A male subject · a dermoscopic view of a skin lesion.
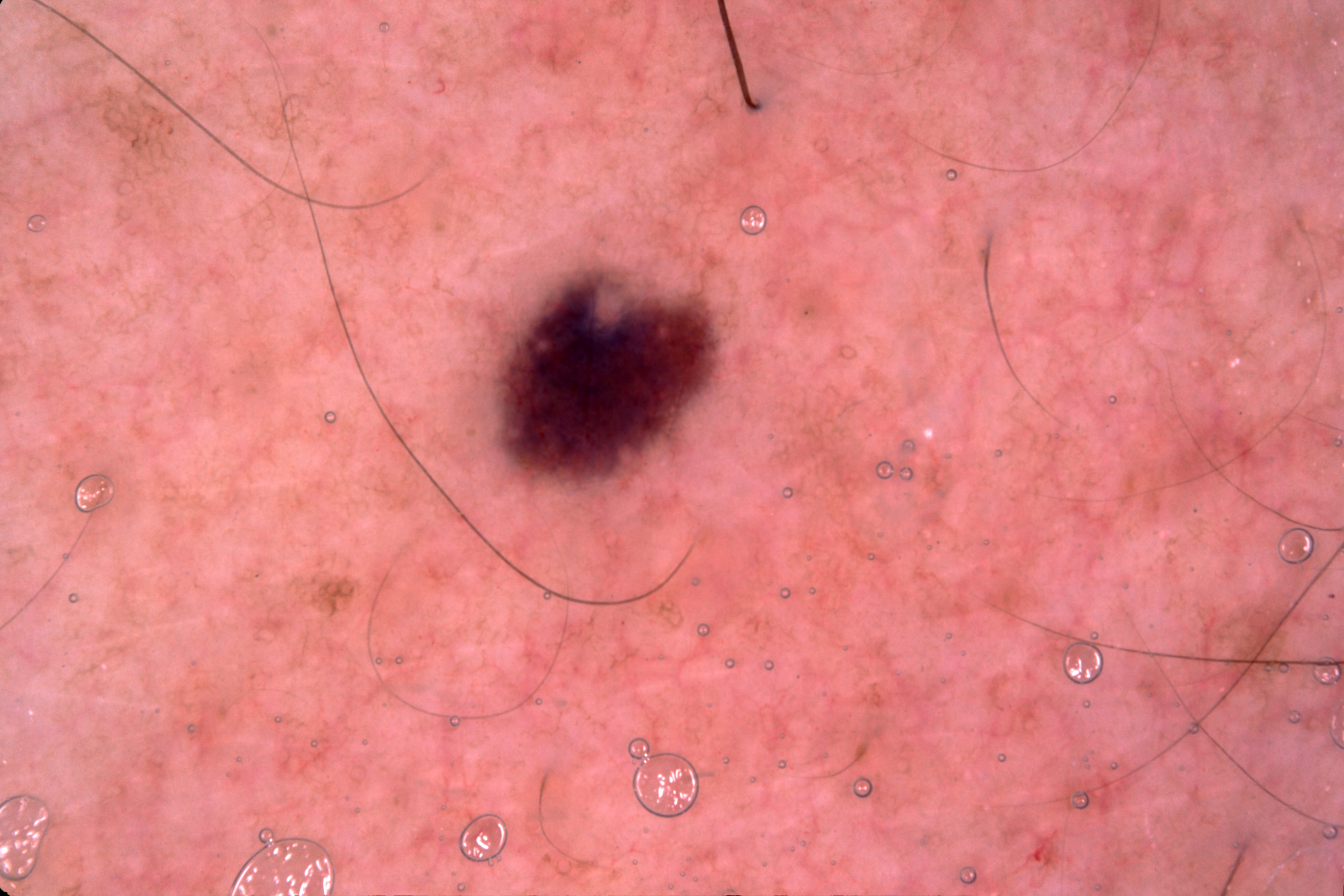dermoscopic features assessed but absent = milia-like cysts, streaks, pigment network, and negative network | location = <box>489, 263, 721, 497</box> | diagnostic label = a melanocytic nevus, a benign lesion.